The lesion is associated with itching; the photo was captured at an angle; the affected area is the leg: 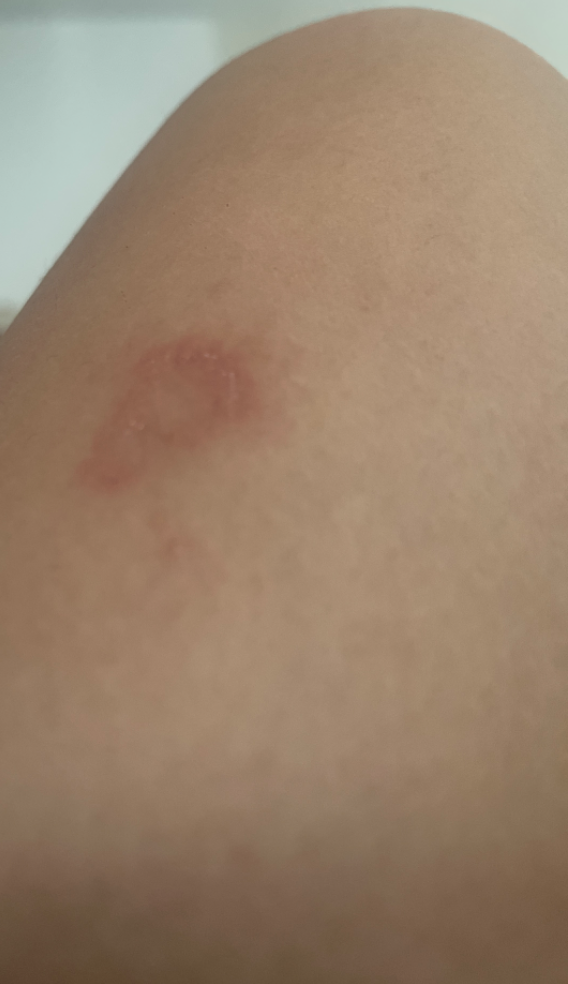assessment = unable to determine.